The affected area is the arm · female contributor, age 30–39 · an image taken at a distance: 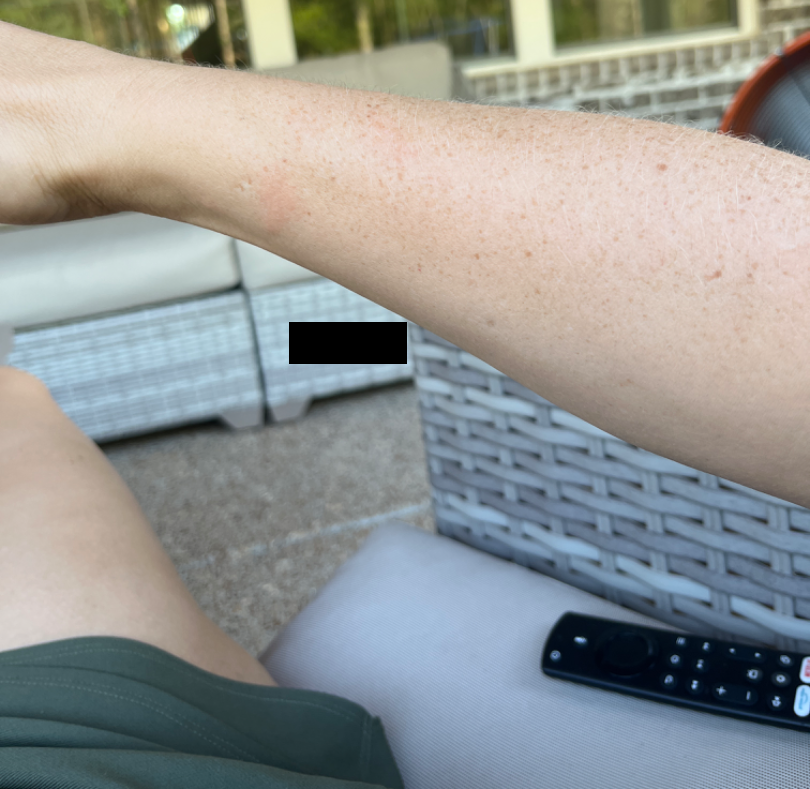dermatologist impression: the differential includes Eczema and Allergic Contact Dermatitis, with no clear leading consideration.